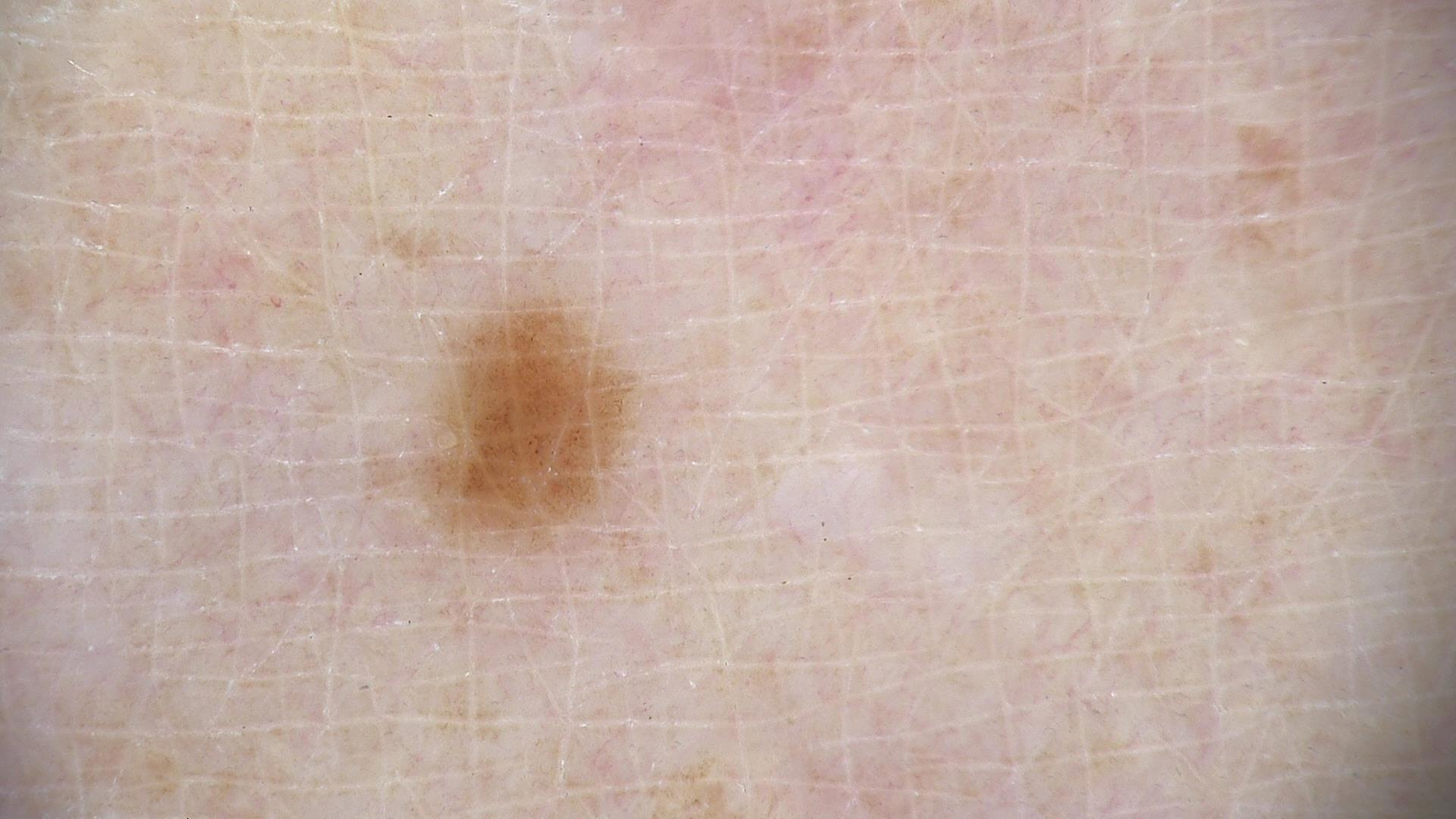{
  "image": "dermatoscopy",
  "diagnosis": {
    "name": "junctional nevus",
    "code": "jb",
    "malignancy": "benign",
    "super_class": "melanocytic",
    "confirmation": "expert consensus"
  }
}